A dermoscopic photograph of a skin lesion.
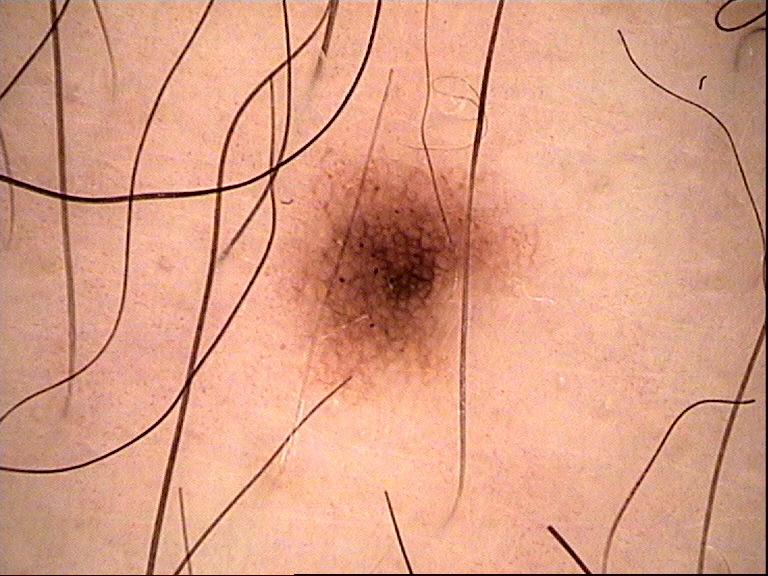class=dysplastic junctional nevus (expert consensus).